A dermoscopic photograph of a skin lesion: 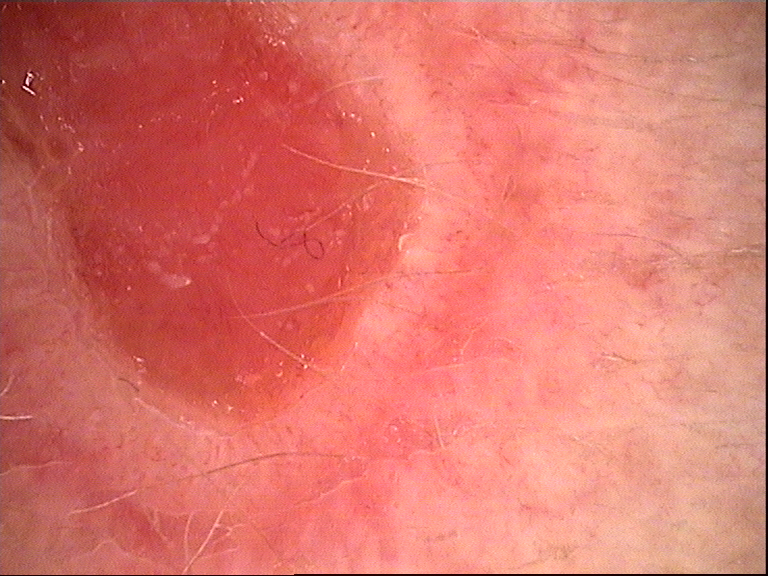Summary:
This is a keratinocytic lesion.
Pathology:
The biopsy diagnosis was a squamous cell carcinoma.